Dermoscopy of a skin lesion.
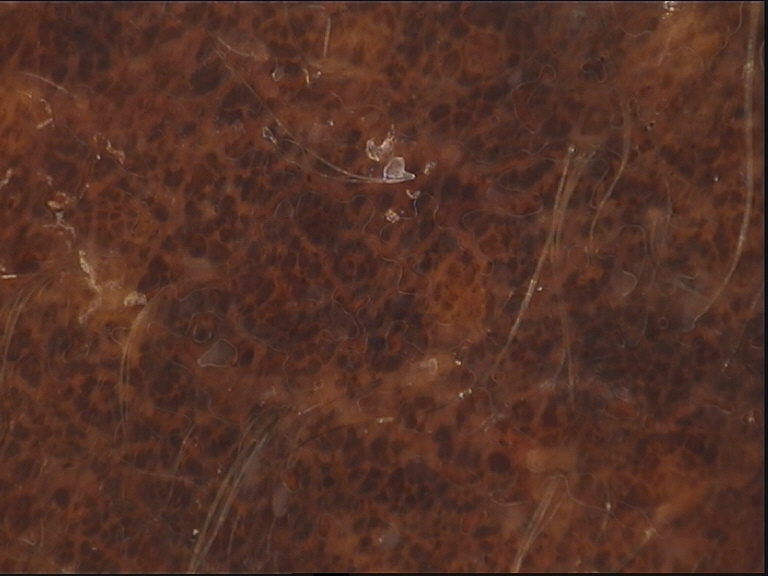Case:
– category — banal
– assessment — congenital compound nevus (expert consensus)